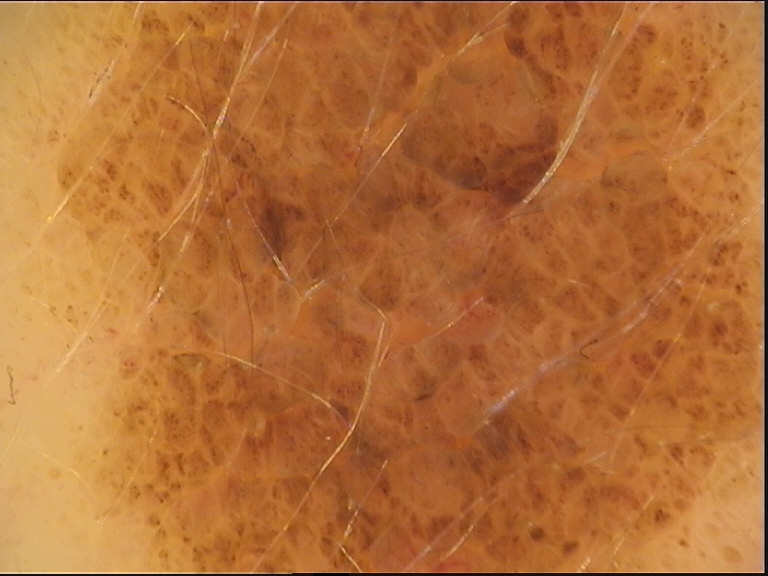The diagnostic label was a congenital compound nevus.